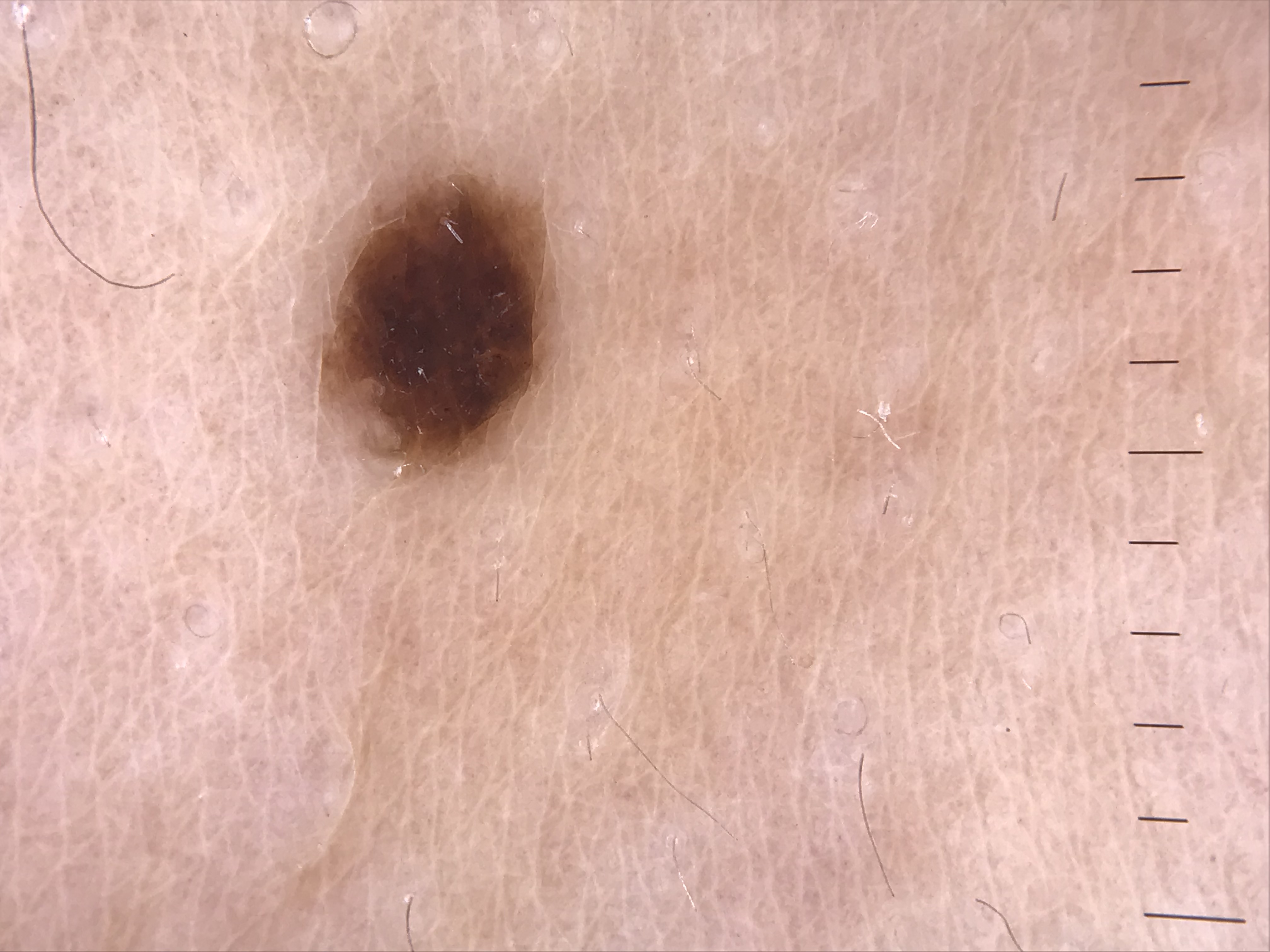| key | value |
|---|---|
| category | banal |
| class | junctional nevus (expert consensus) |